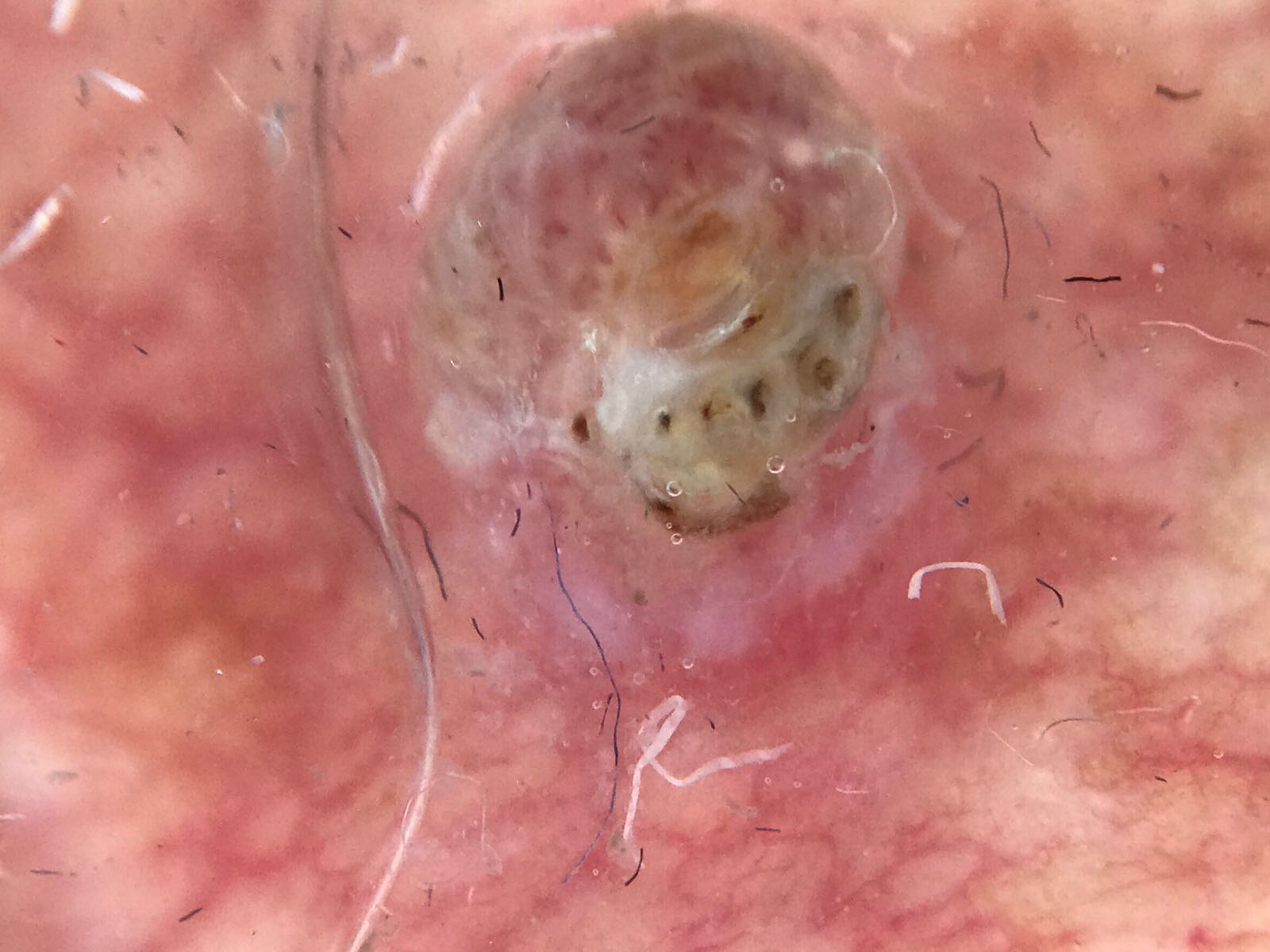  image: dermatoscopy
  lesion_type:
    main_class: keratinocytic
  diagnosis:
    name: squamous cell carcinoma
    code: scc
    malignancy: malignant
    super_class: non-melanocytic
    confirmation: histopathology